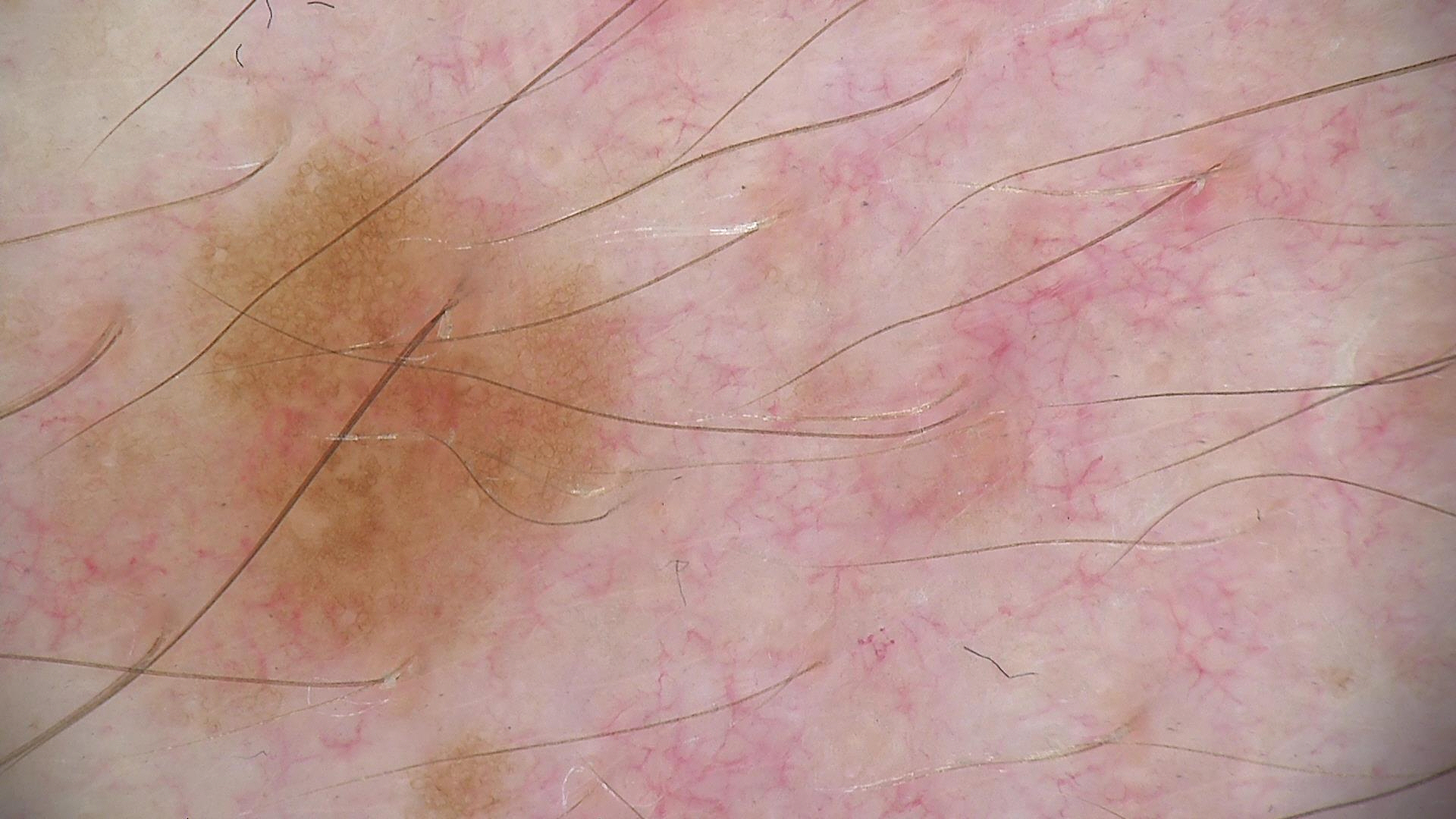The diagnostic label was a dysplastic junctional nevus.